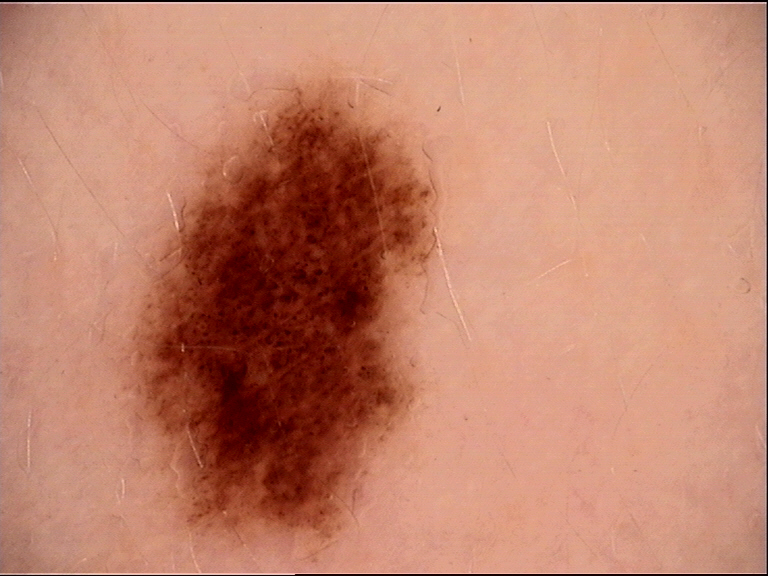Summary:
A skin lesion imaged with a dermatoscope.
Conclusion:
The diagnostic label was a benign lesion — a dysplastic junctional nevus.